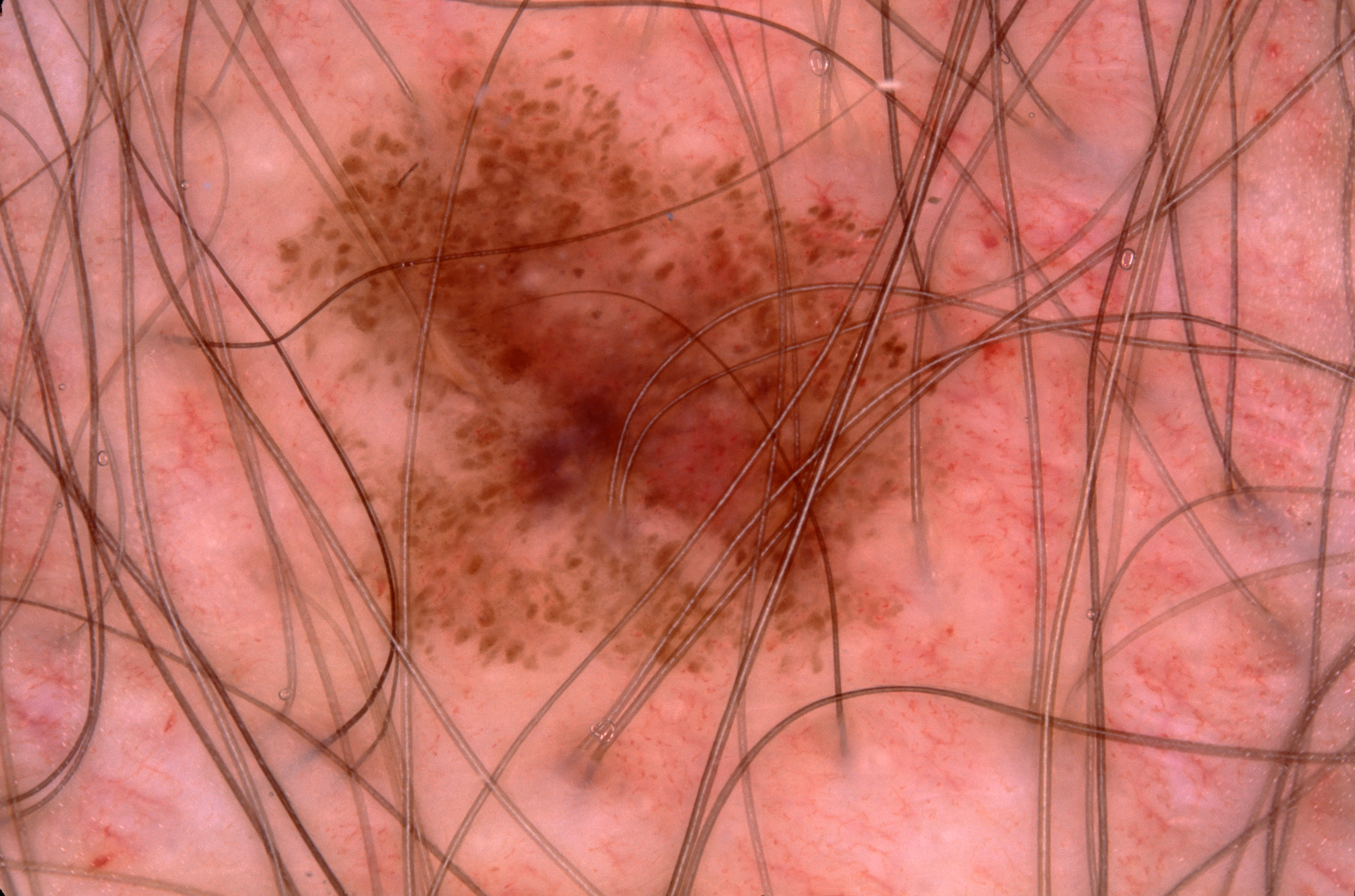A dermoscopic image of a skin lesion.
A male subject approximately 30 years of age.
The lesion's extent is left=234, top=23, right=1017, bottom=711.
The dermoscopic pattern shows no streaks, negative network, milia-like cysts, or pigment network.
The clinical diagnosis was a melanocytic nevus.